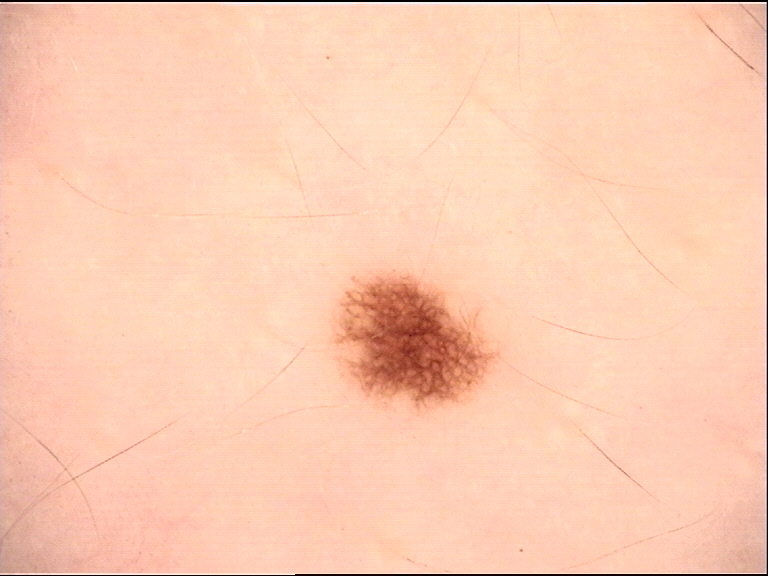* modality: dermatoscopy
* class: junctional nevus (expert consensus)